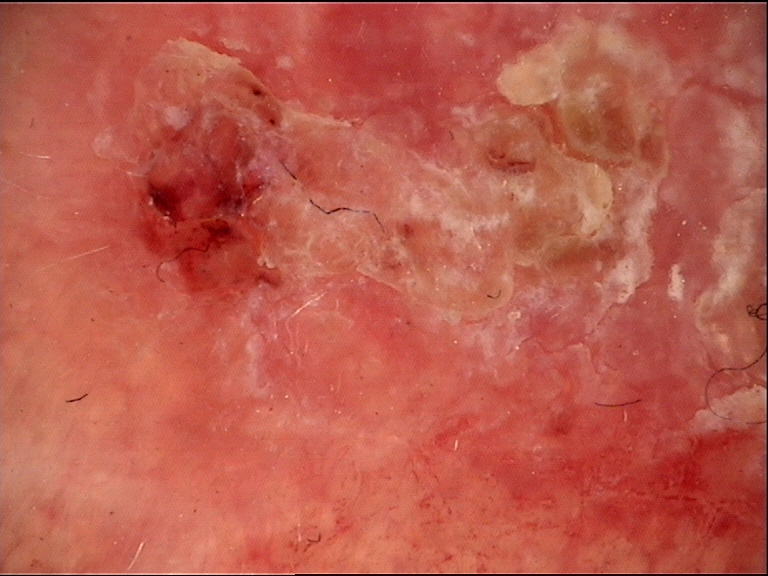Pathology:
The biopsy diagnosis was a keratinocytic lesion — a squamous cell carcinoma.